A female subject aged 73-77, a dermoscopic image of a skin lesion.
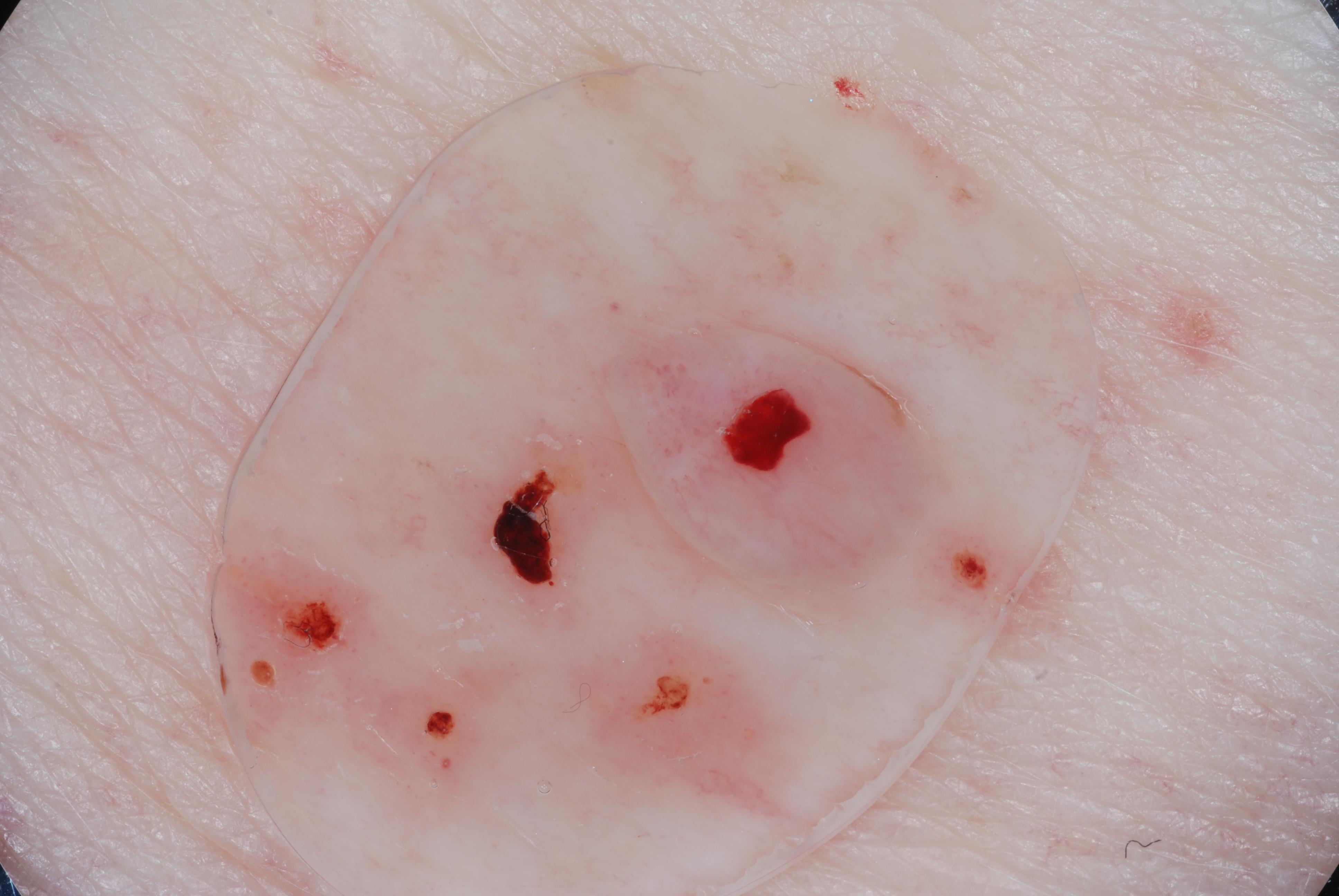{"dermoscopic_features": {"present": [], "absent": ["negative network", "streaks", "milia-like cysts", "pigment network"]}, "lesion_location": {"bbox_xyxy": [583, 283, 1037, 663]}, "diagnosis": {"name": "melanocytic nevus", "malignancy": "benign", "lineage": "melanocytic", "provenance": "clinical"}}